A female patient aged 53 to 57 · dermoscopy of a skin lesion: 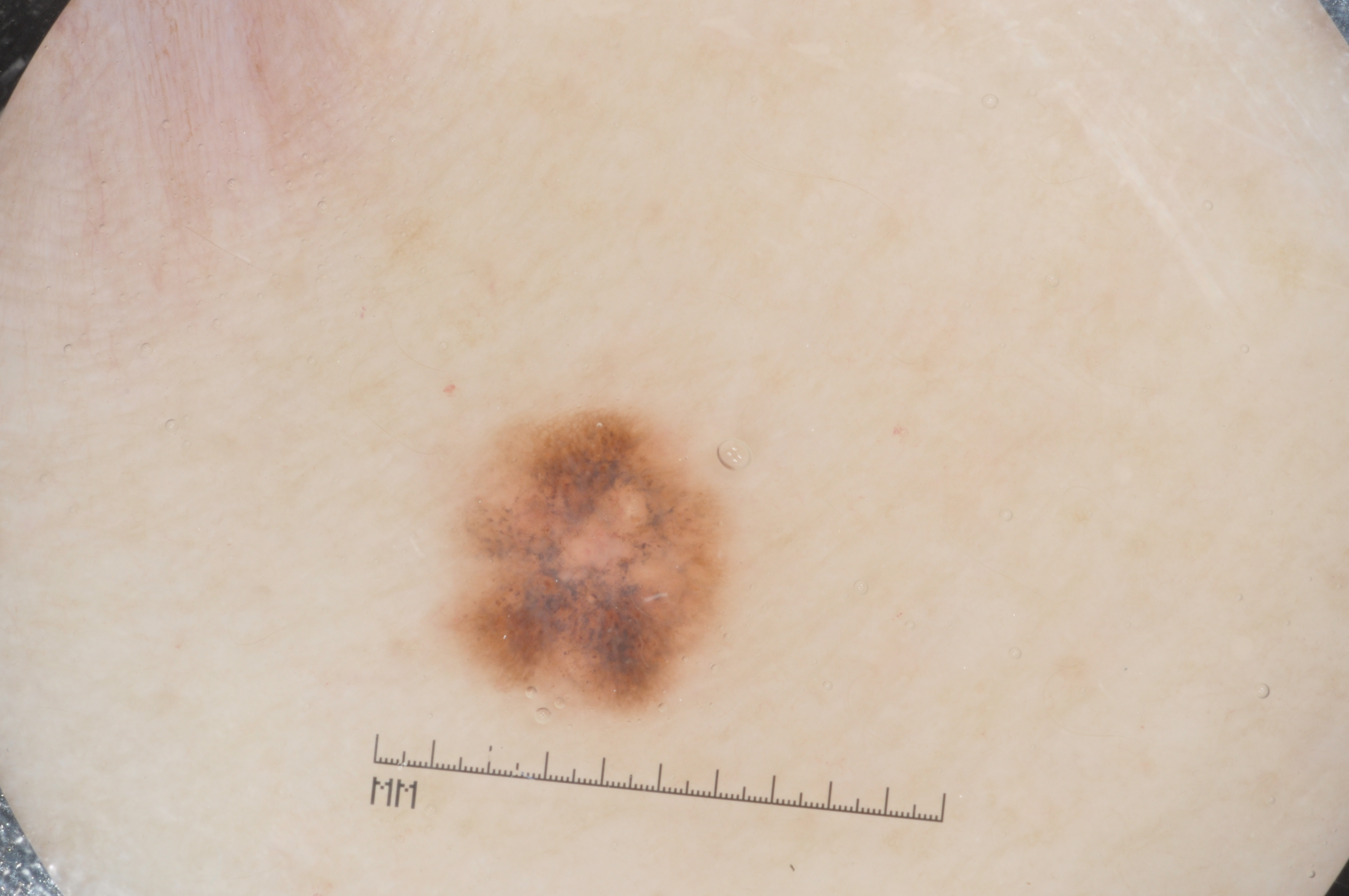lesion extent — ~6% of the field
location — bbox(443, 406, 738, 714)
dermoscopic features — milia-like cysts and pigment network
impression — a melanoma